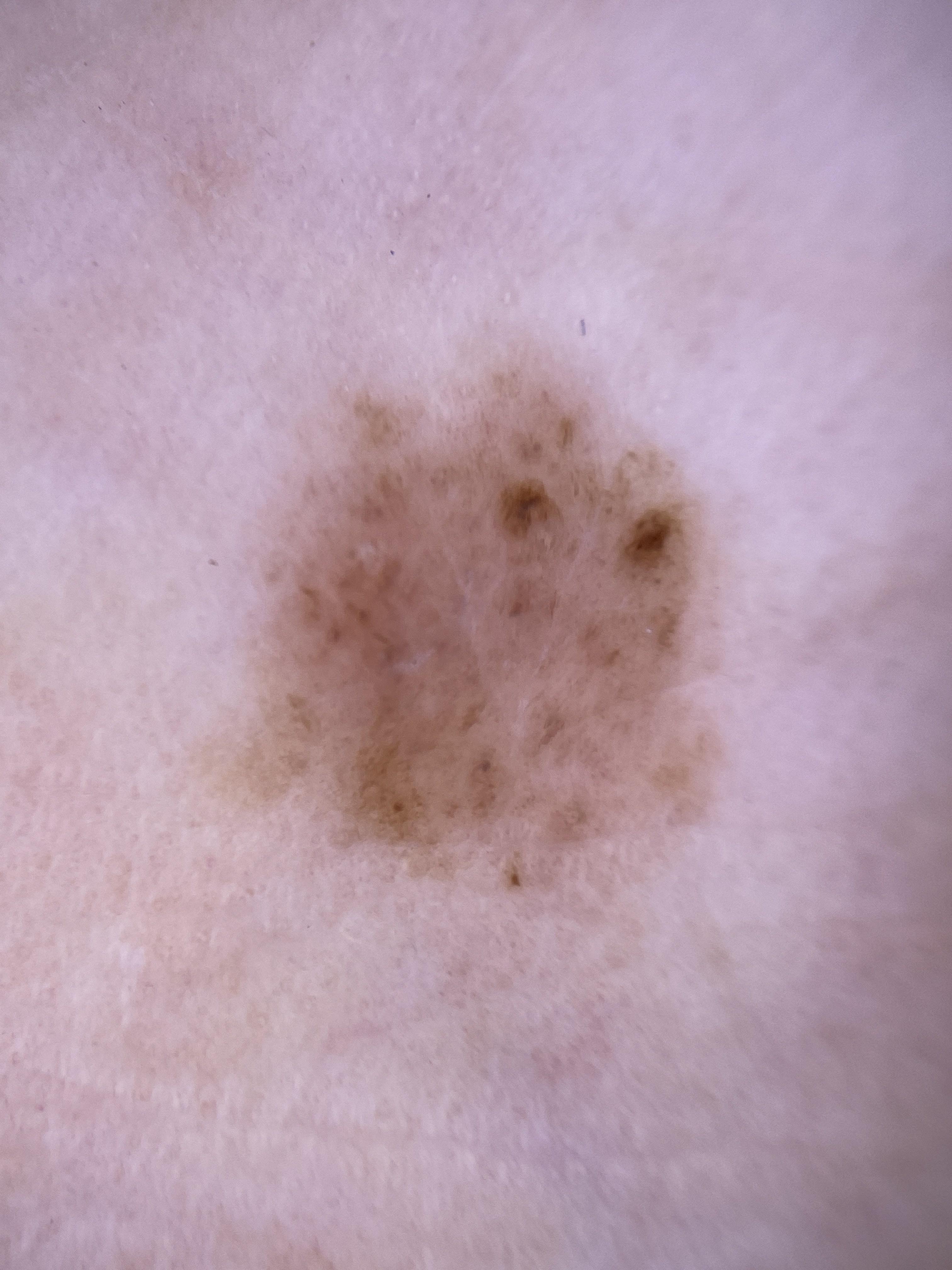A female subject aged 33 to 37.
The lesion involves a lower extremity.
Histopathology confirmed a benign, melanocytic lesion — a nevus.